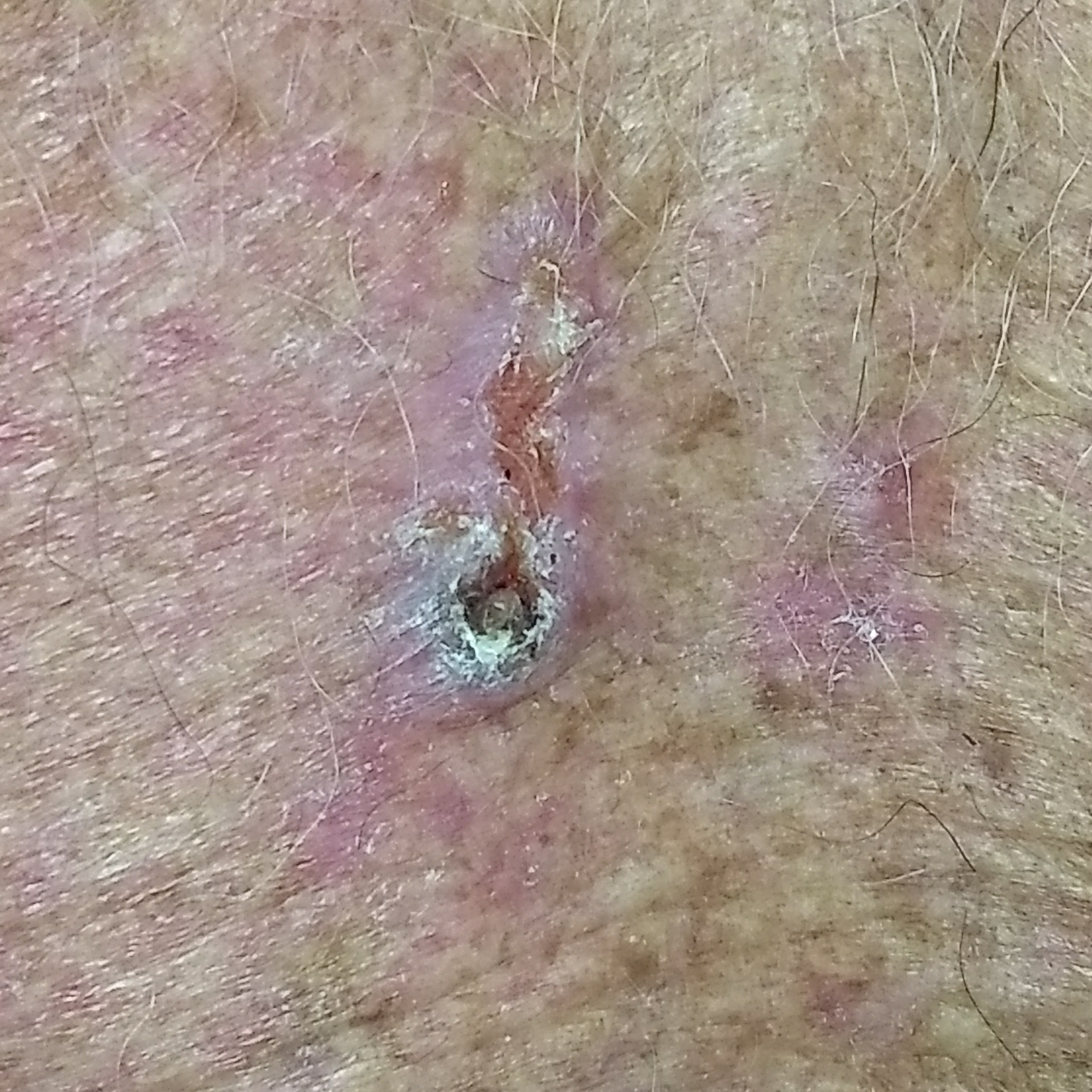<record>
  <risk_factors>
    <positive>prior cancer (patient or family), pesticide exposure</positive>
    <negative>smoking</negative>
  </risk_factors>
  <image>clinical photograph</image>
  <patient>
    <age>83</age>
    <gender>male</gender>
  </patient>
  <lesion_location>the chest</lesion_location>
  <symptoms>
    <present>growth, bleeding, itching, pain, elevation</present>
  </symptoms>
  <diagnosis>
    <name>basal cell carcinoma</name>
    <code>BCC</code>
    <malignancy>malignant</malignancy>
    <confirmation>histopathology</confirmation>
  </diagnosis>
</record>